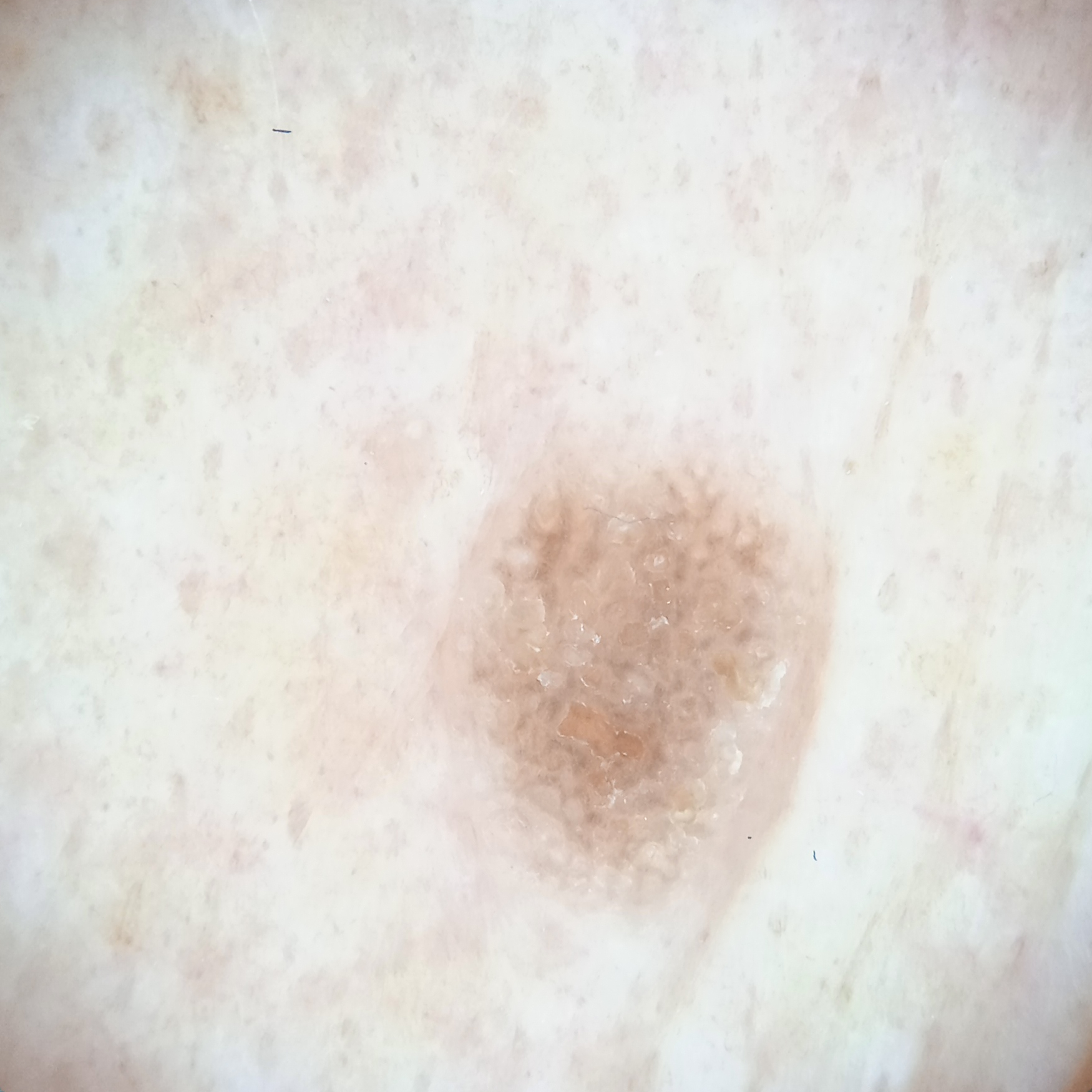Case summary:
The patient reports no sunbed use. A female subject 81 years old. Dermoscopy of a skin lesion. Acquired for a research image collection, with no referral diagnosis. The patient says their skin reddens painfully with sun exposure.
Conclusion:
The dermatologists' assessment was a seborrheic keratosis.